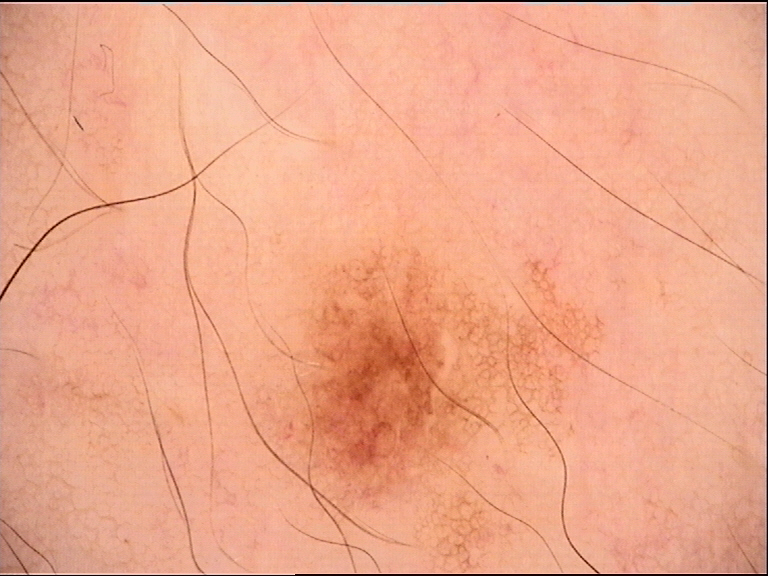Q: What is the diagnosis?
A: dysplastic junctional nevus (expert consensus)